Close-up view; female contributor, age 18–29; the lesion involves the sole of the foot, top or side of the foot, arm, palm, back of the hand and leg:
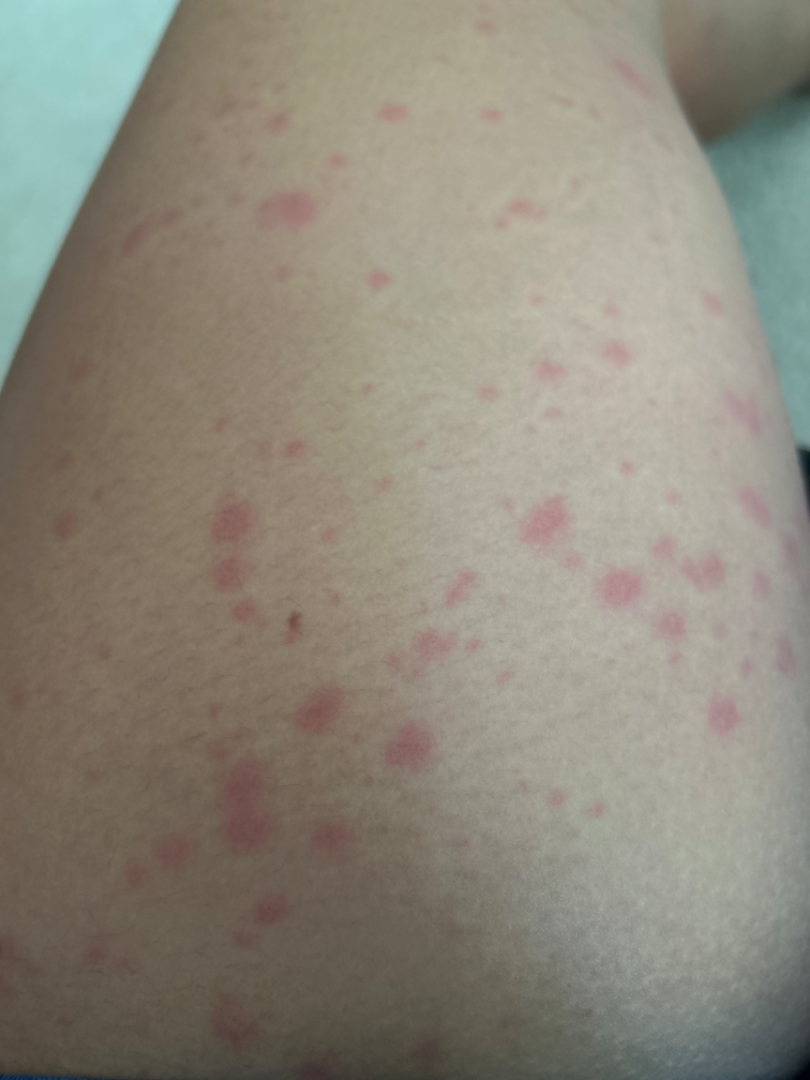Q: How does the lesion feel?
A: raised or bumpy
Q: When did this start?
A: about one day
Q: What is the dermatologist's impression?
A: most consistent with Urticaria